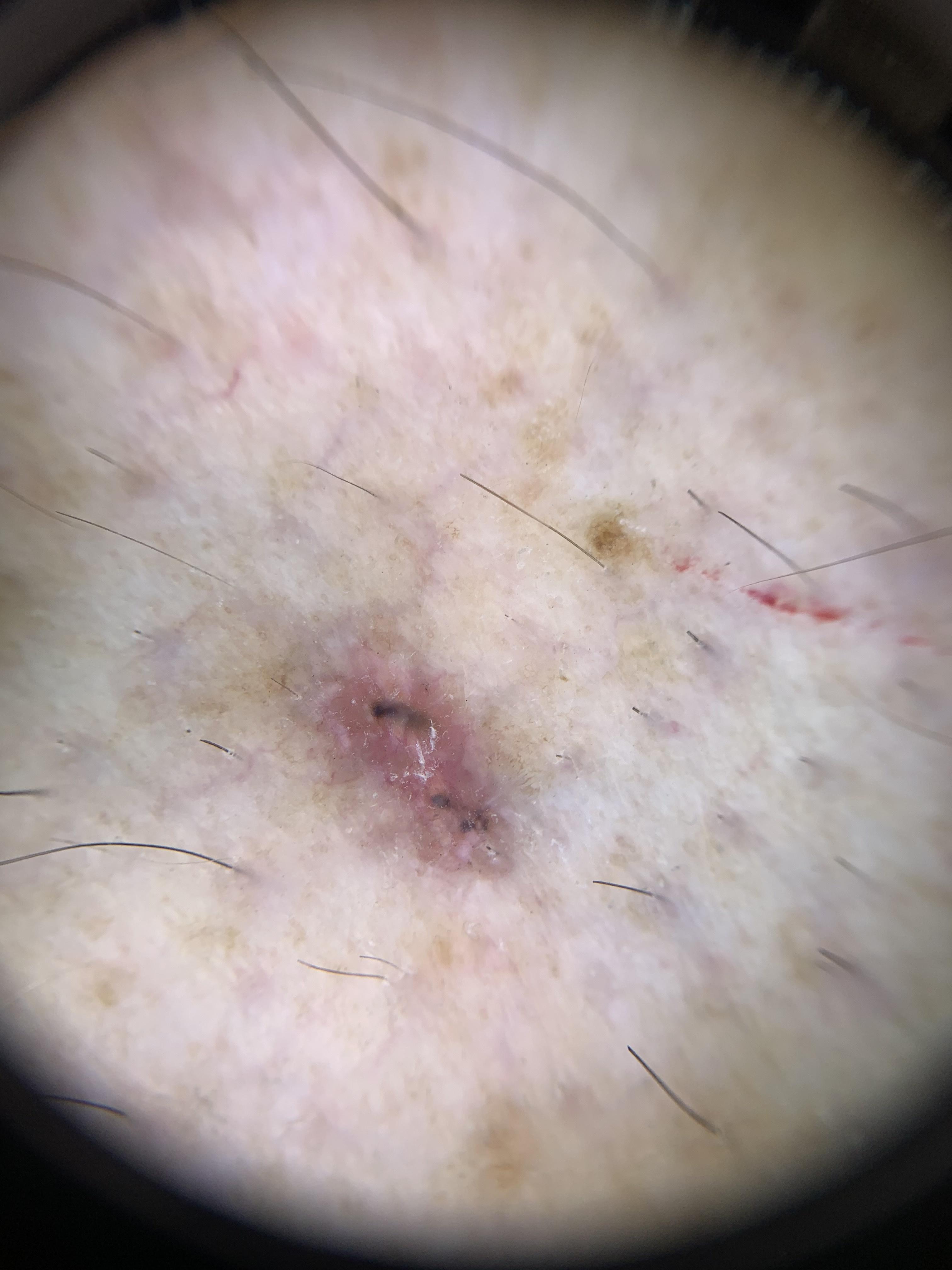Case summary:
A skin lesion imaged with a dermatoscope. Recorded as Fitzpatrick skin type II. The lesion is on a lower extremity.
Conclusion:
Confirmed on histopathology as a basal cell carcinoma.